On a questionnaire the patient reported a personal history of cancer, a personal history of skin cancer, no sunbed use, and no immunosuppression; the patient says their skin tans without first burning; the patient describes having a moderate number of moles; a female patient 75 years old; collected as part of a research study, without a referral diagnosis: 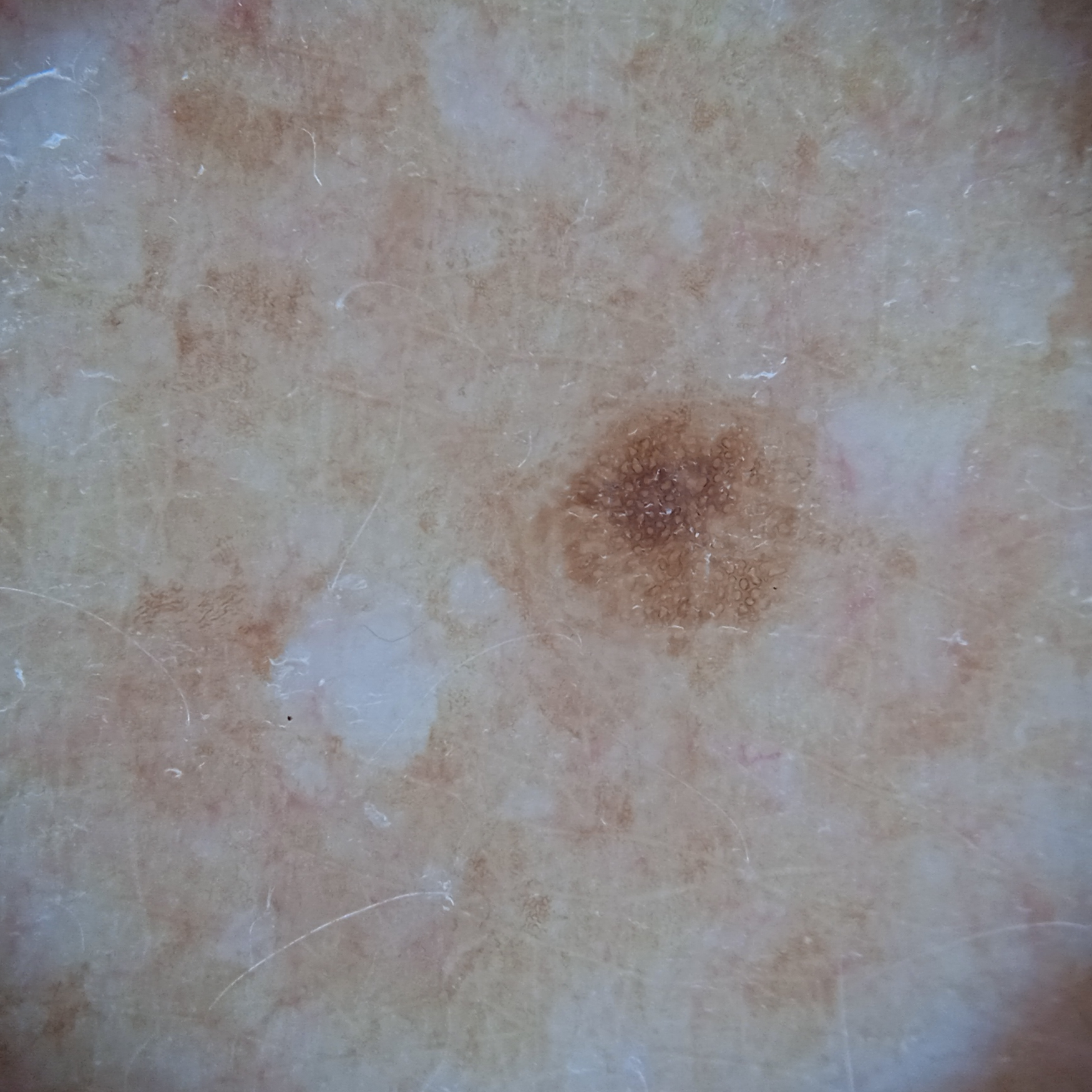Q: What is the anatomic site?
A: the back
Q: What was the diagnosis?
A: melanocytic nevus (dermatologist consensus)